The contributor is a female aged 70–79, the affected area is the arm, this image was taken at a distance: 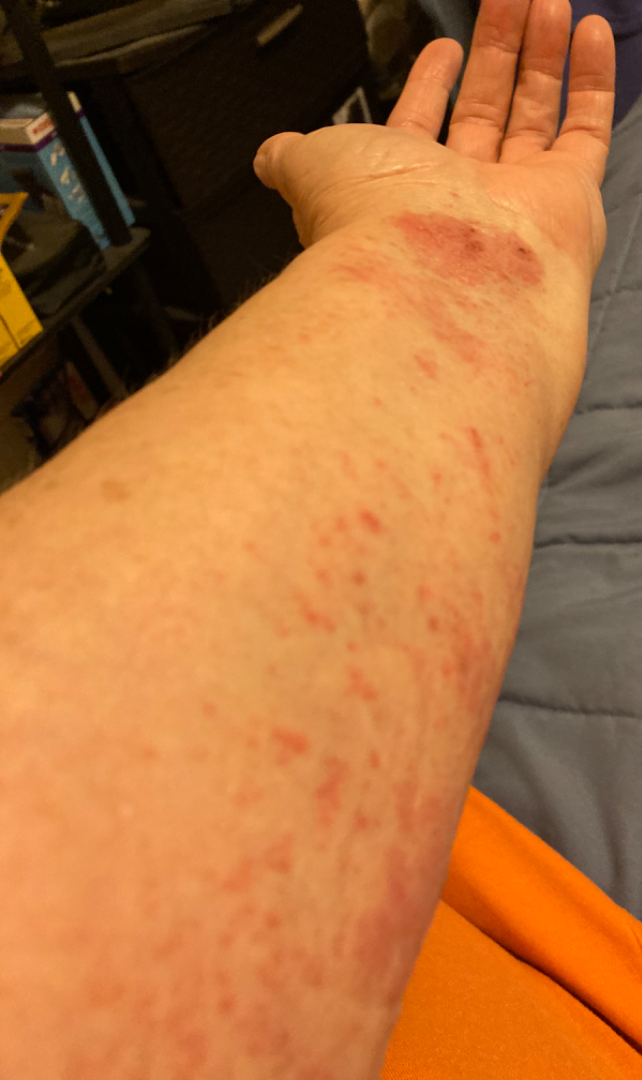Findings: The reviewing panel's impression was: favoring Allergic Contact Dermatitis; also raised was Crusted eczematous dermatitis; with consideration of Eczema; less probable is Secondary impetiginization.